A dermoscopic photograph of a skin lesion:
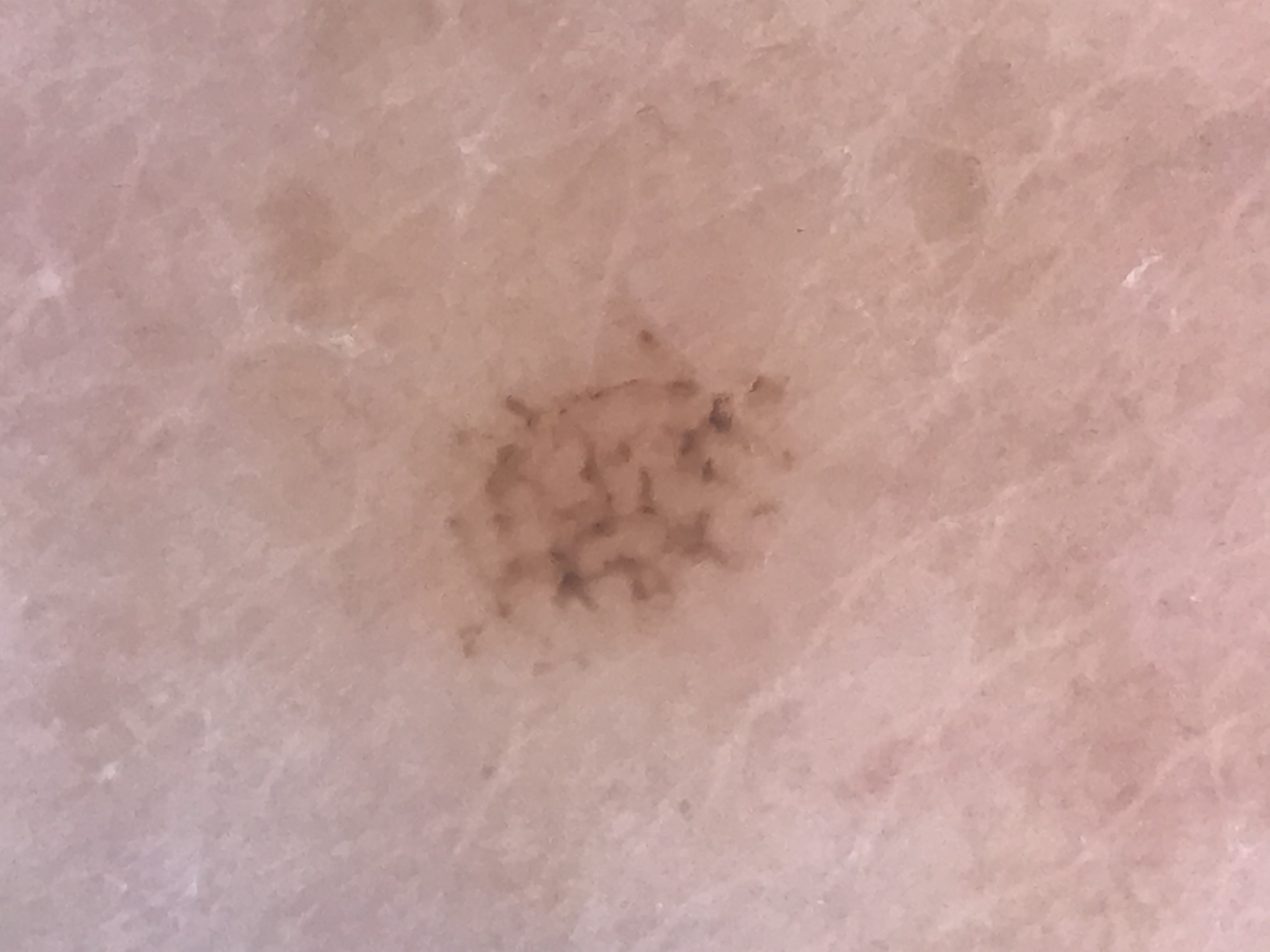Classified as a benign lesion — an acral dysplastic junctional nevus.